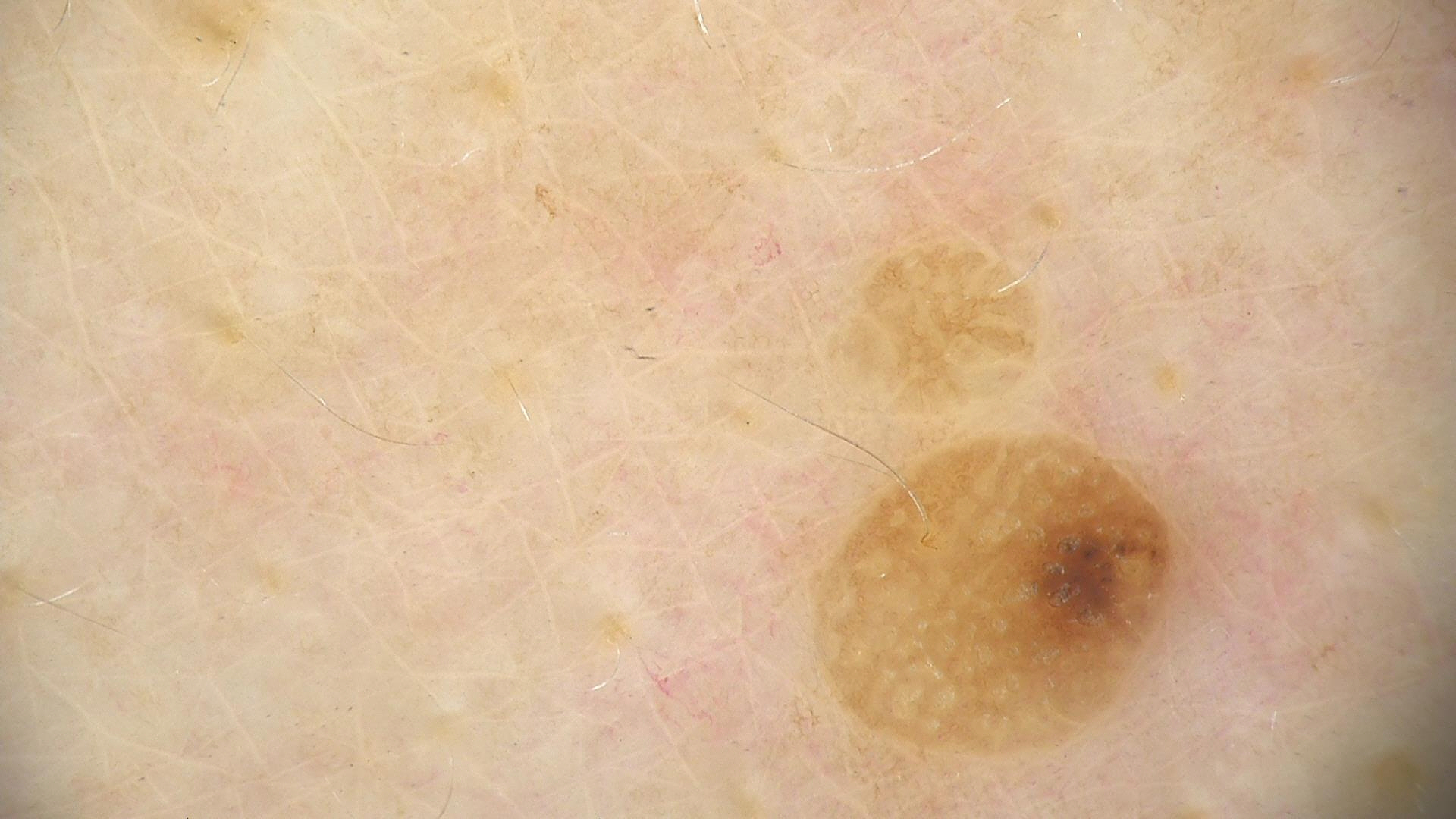Q: How is the lesion classified?
A: keratinocytic
Q: What was the diagnostic impression?
A: seborrheic keratosis (expert consensus)